The lesion involves the arm · a close-up photograph.
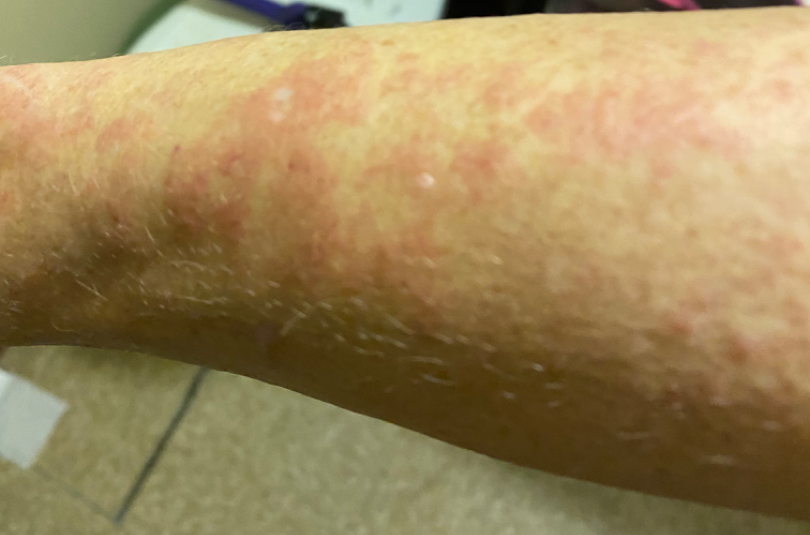assessment=indeterminate